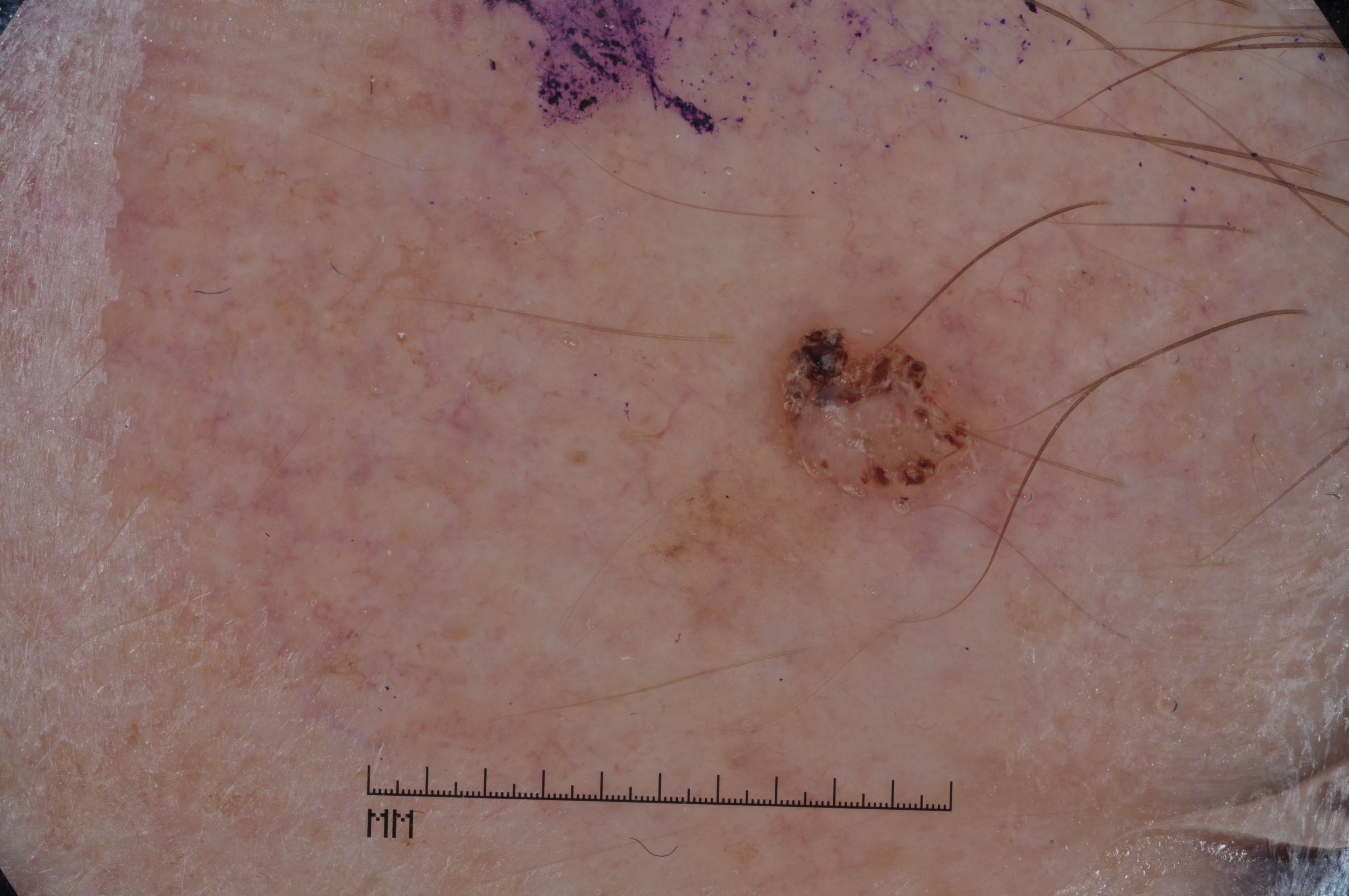A male patient approximately 60 years of age. A dermoscopy image of a single skin lesion. On dermoscopy, the lesion shows milia-like cysts. The lesion is located at [766, 303, 1007, 508]. A small lesion occupying a minor part of the field. Consistent with a seborrheic keratosis, a benign lesion.